The photograph is a close-up of the affected area · located on the top or side of the foot · male contributor, age 18–29.
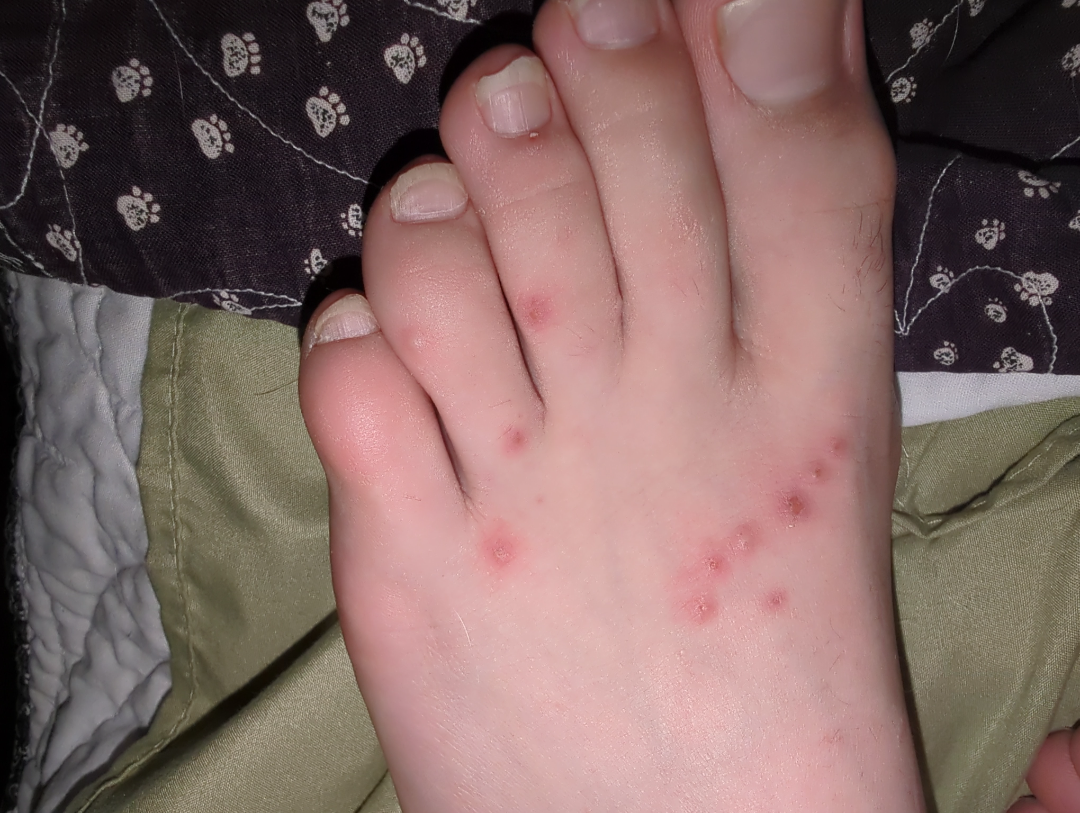duration: one to four weeks
skin tone: FST II; human graders estimated MST 1–2
patient describes the issue as: a rash
diagnostic considerations: consistent with Insect Bite